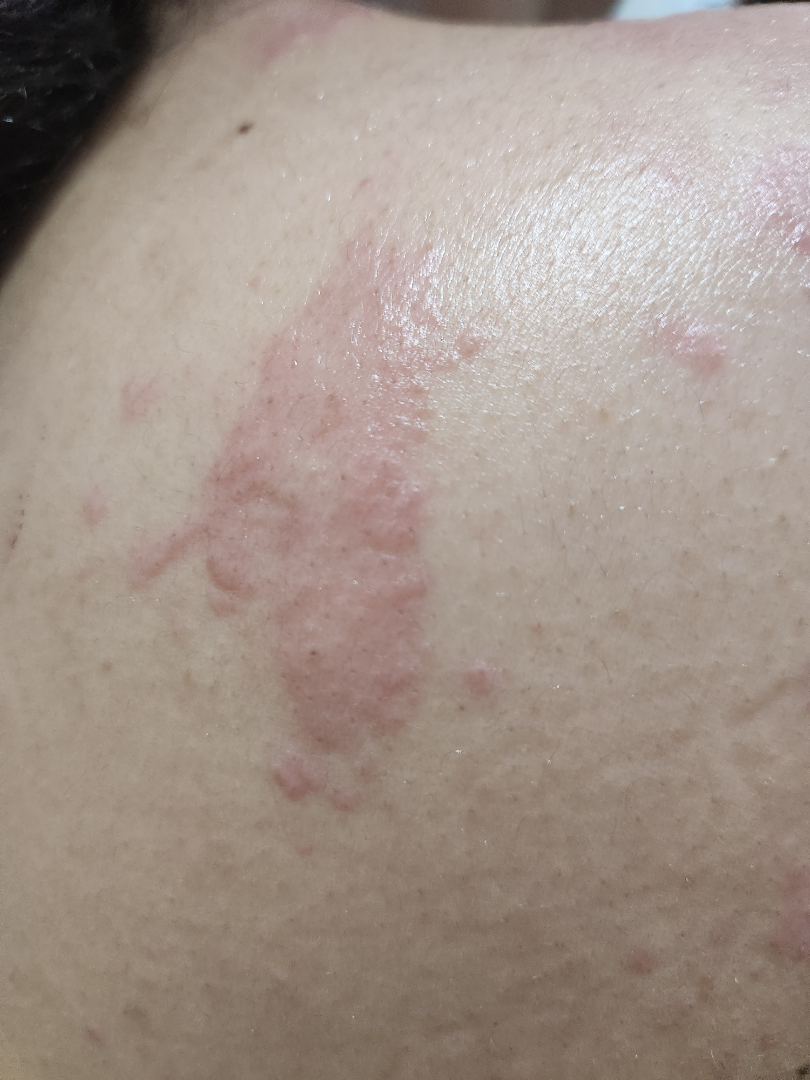  texture: raised or bumpy
  symptoms:
    - itching
    - burning
  duration: less than one week
  body_site:
    - palm
    - leg
    - head or neck
    - back of the hand
    - top or side of the foot
    - front of the torso
    - sole of the foot
    - arm
  shot_type: at an angle
  skin_tone:
    fitzpatrick: III
    monk_skin_tone:
      - 2
      - 4
  differential:
    leading:
      - Allergic Contact Dermatitis
    considered:
      - Herpes Zoster